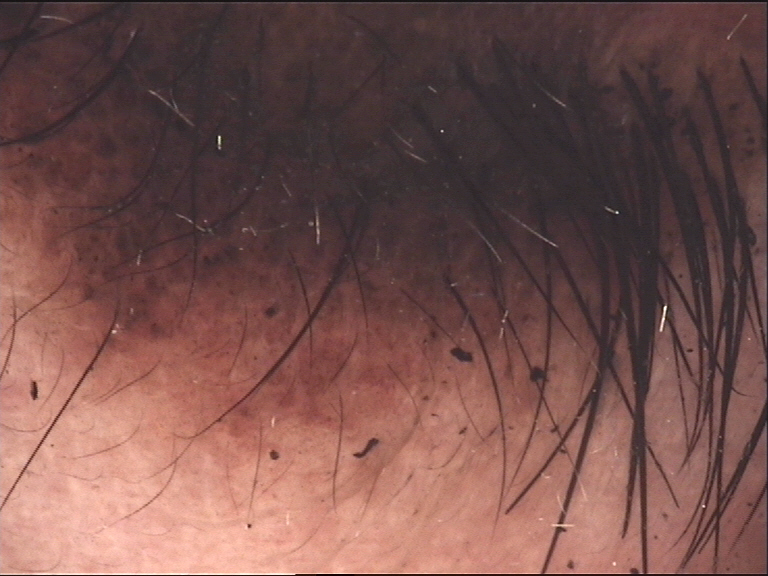Findings: This is a banal lesion. Conclusion: The diagnostic label was a congenital compound nevus.